A dermatoscopic image of a skin lesion; a female subject aged around 75.
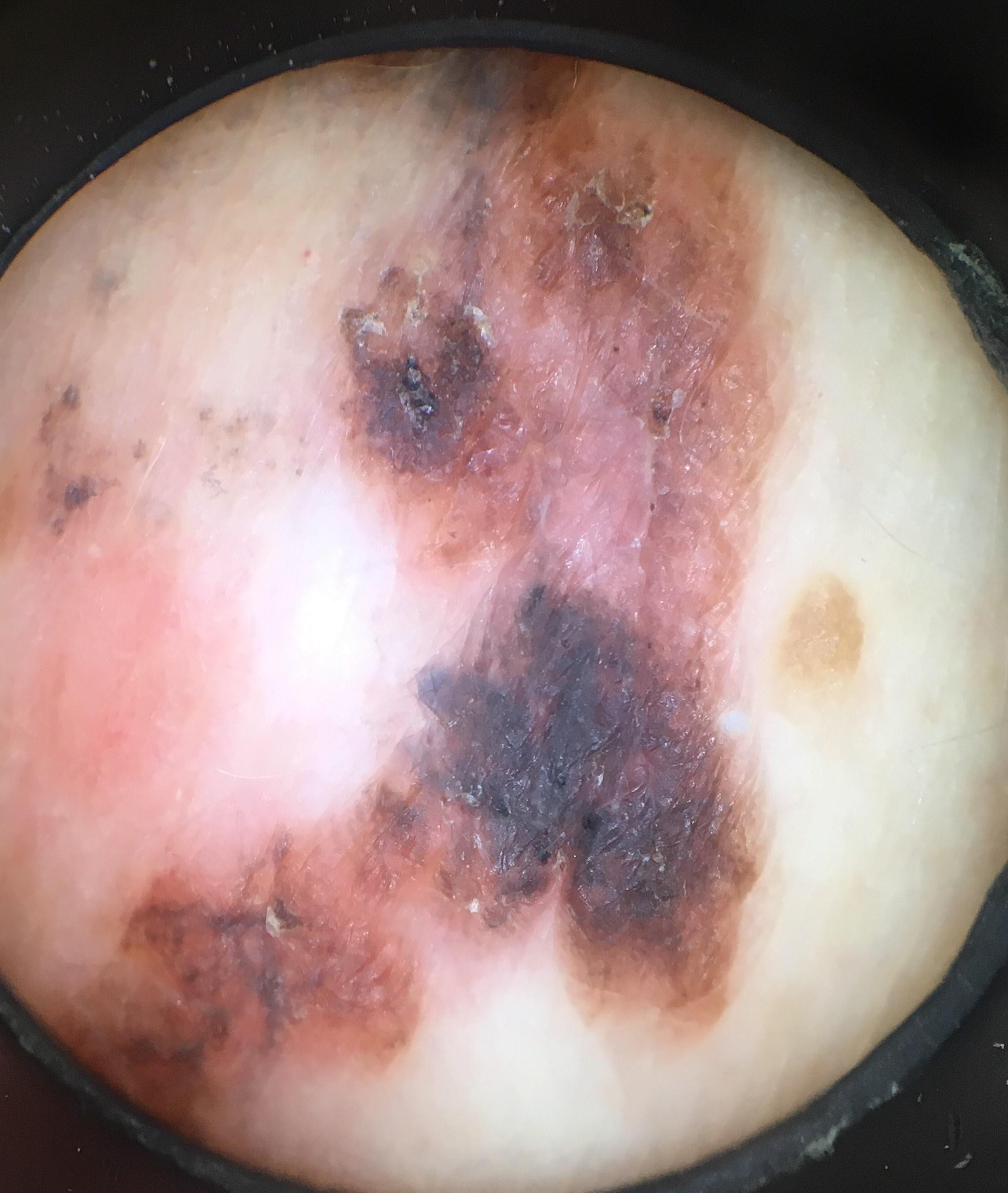On biopsy, the diagnosis was a melanoma.